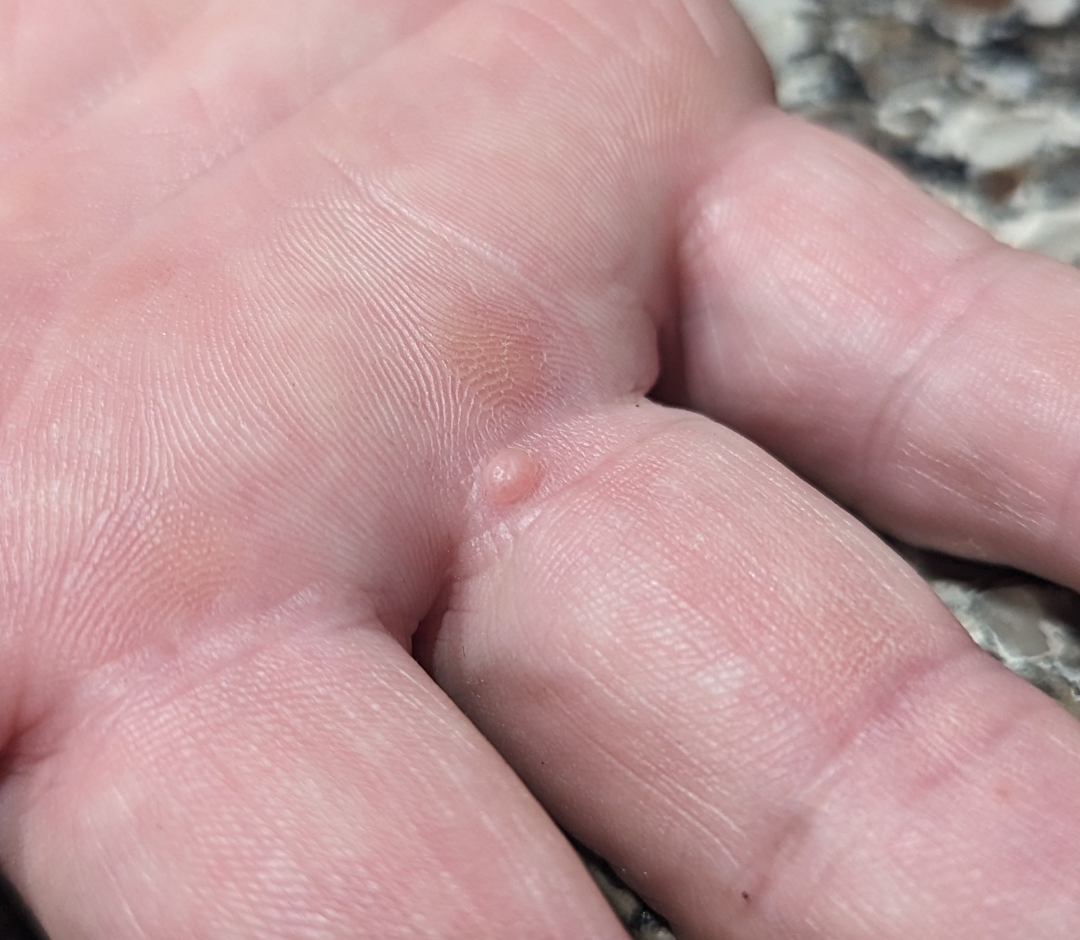On independent review by the dermatologists, favoring Melanocytic Nevus; also raised was Verruca vulgaris; less likely is Cyst; less probable is Adnexal neoplasm; a more distant consideration is Acquired digital fibrokeratoma.